A close-up photograph · reported lesion symptoms include itching, darkening, burning, bothersome appearance and pain · the lesion involves the leg · the subject is 50–59, female · texture is reported as raised or bumpy, fluid-filled and rough or flaky · Fitzpatrick V; non-clinician graders estimated MST 9 (US pool) or 7 (India pool) · the condition has been present for three to twelve months: 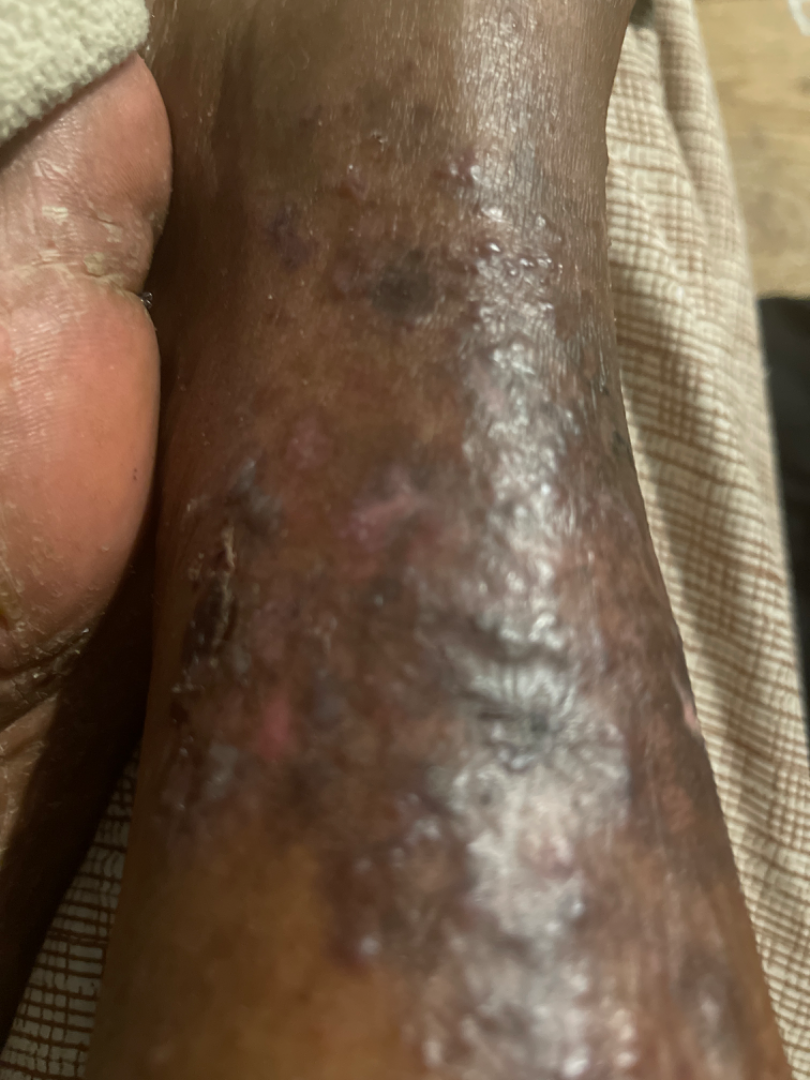impression: most likely Eczema; also consider Stasis Dermatitis; a more distant consideration is Lichen Simplex Chronicus; lower on the differential is Lichen planus/lichenoid eruption.